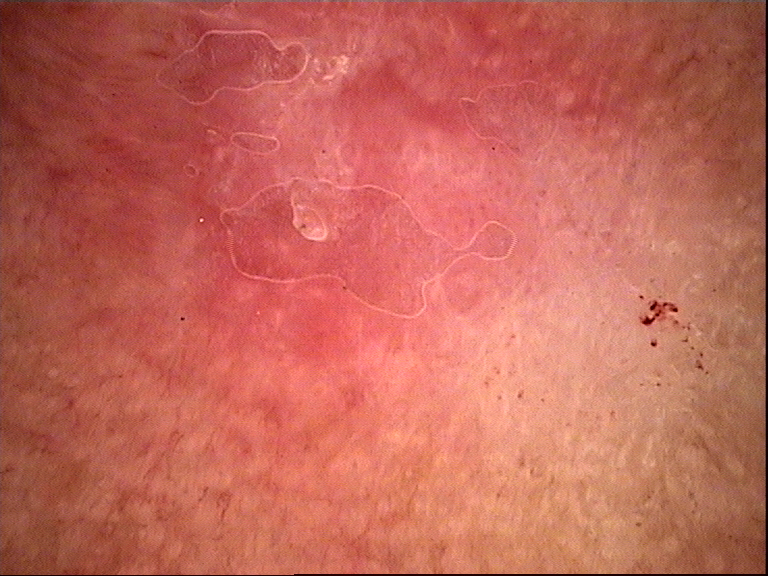Summary: A dermoscopy image of a single skin lesion. The morphology is that of a keratinocytic lesion. Conclusion: Confirmed on histopathology as a malignancy — Bowen's disease.